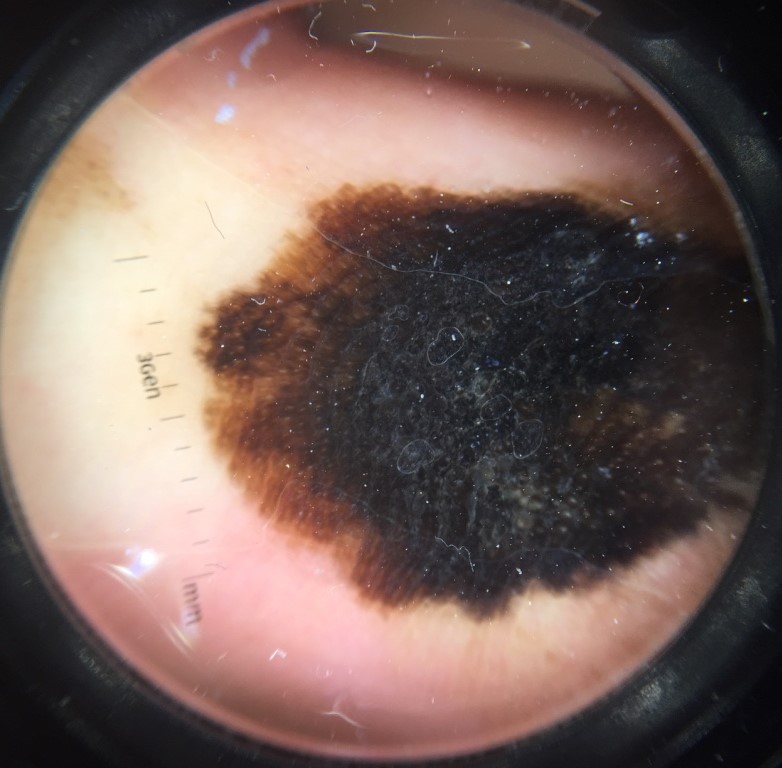A dermoscopic close-up of a skin lesion.
Histopathologically confirmed as an acral lentiginous melanoma.